The affected area is the arm, the photo was captured at an angle:
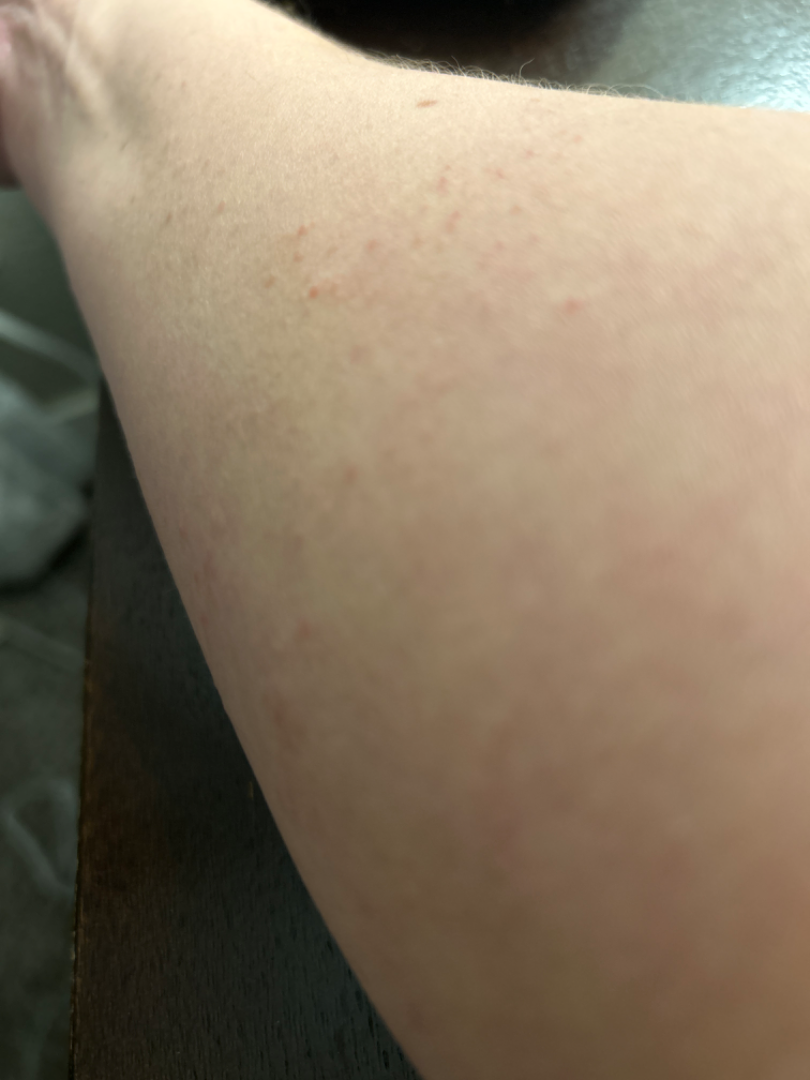duration — less than one week
texture — raised or bumpy
differential diagnosis — most likely Keratosis pilaris